The photo was captured at a distance — 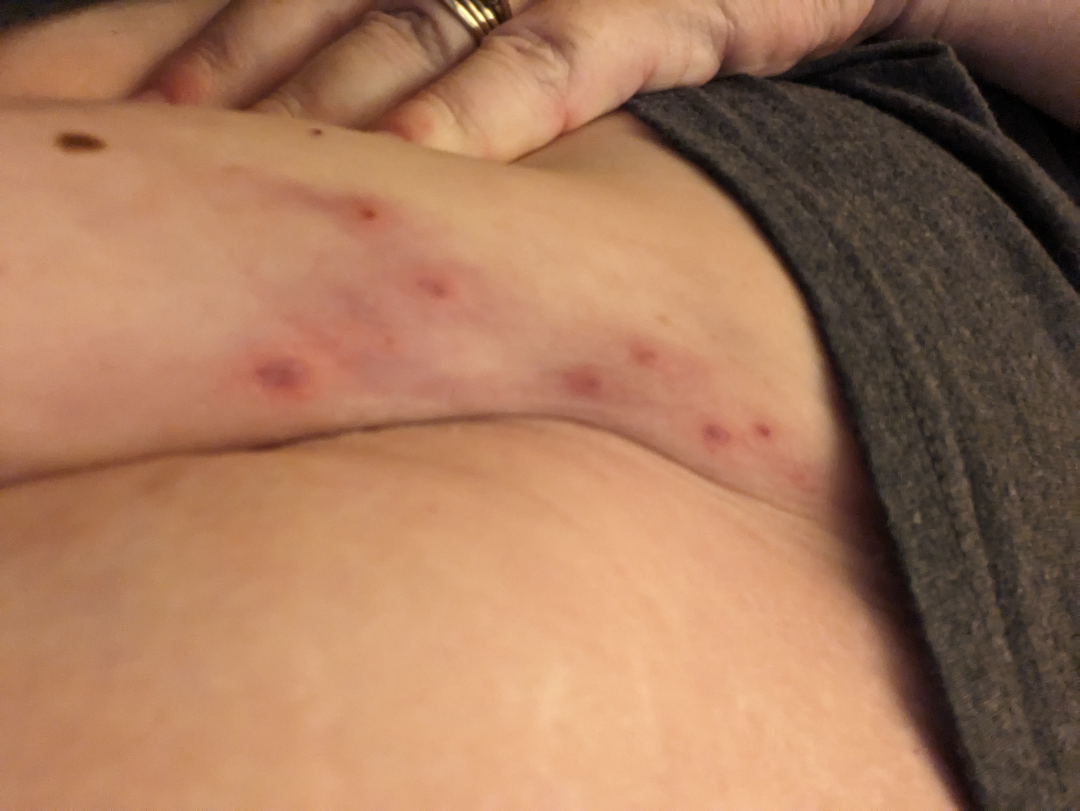| field | value |
|---|---|
| skin tone | Fitzpatrick phototype II |
| self-categorized as | a rash |
| lesion symptoms | itching |
| impression | Herpes Zoster (1.00) |